A dermoscopic photograph of a skin lesion.
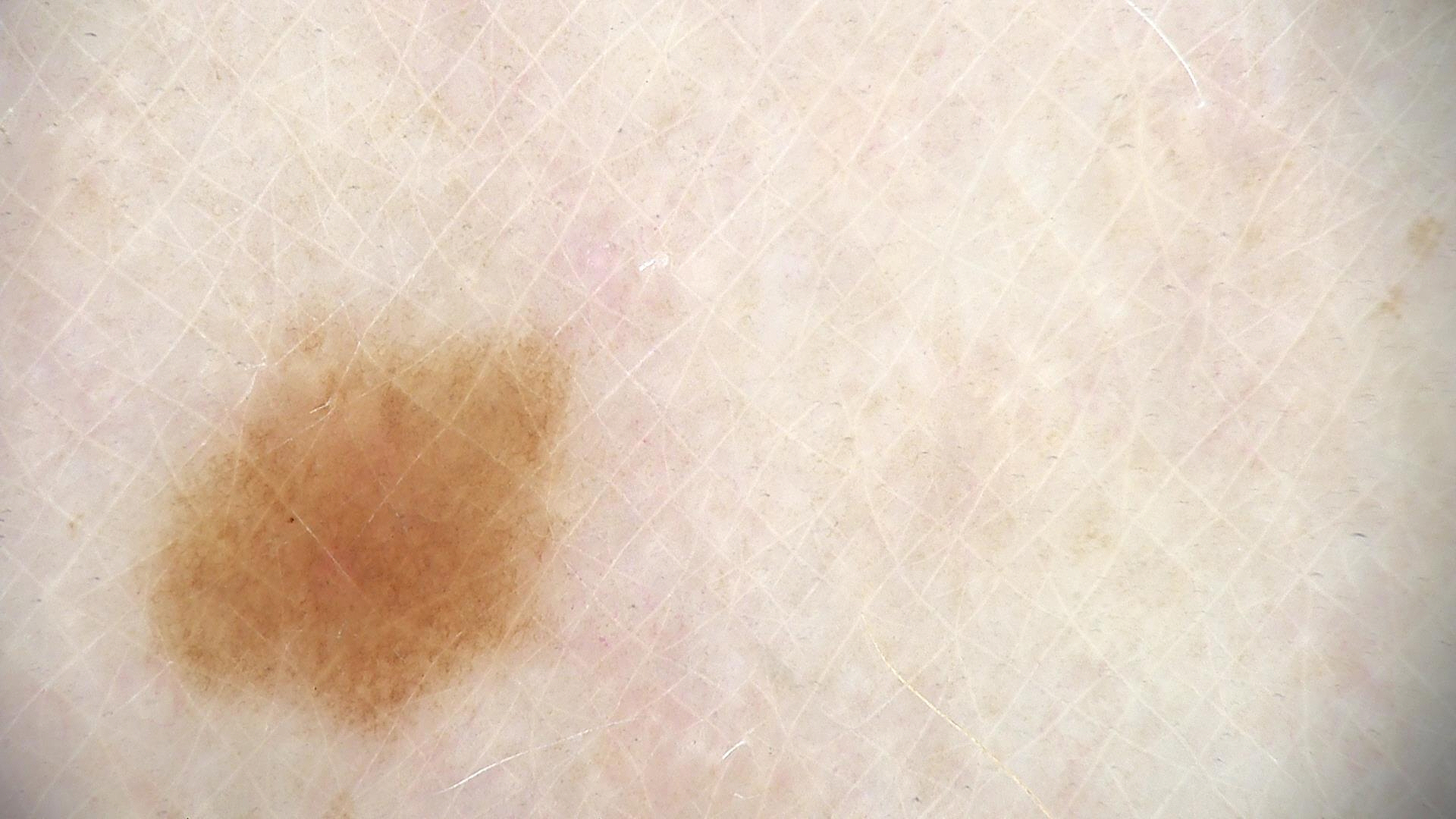| key | value |
|---|---|
| diagnostic label | dysplastic junctional nevus (expert consensus) |